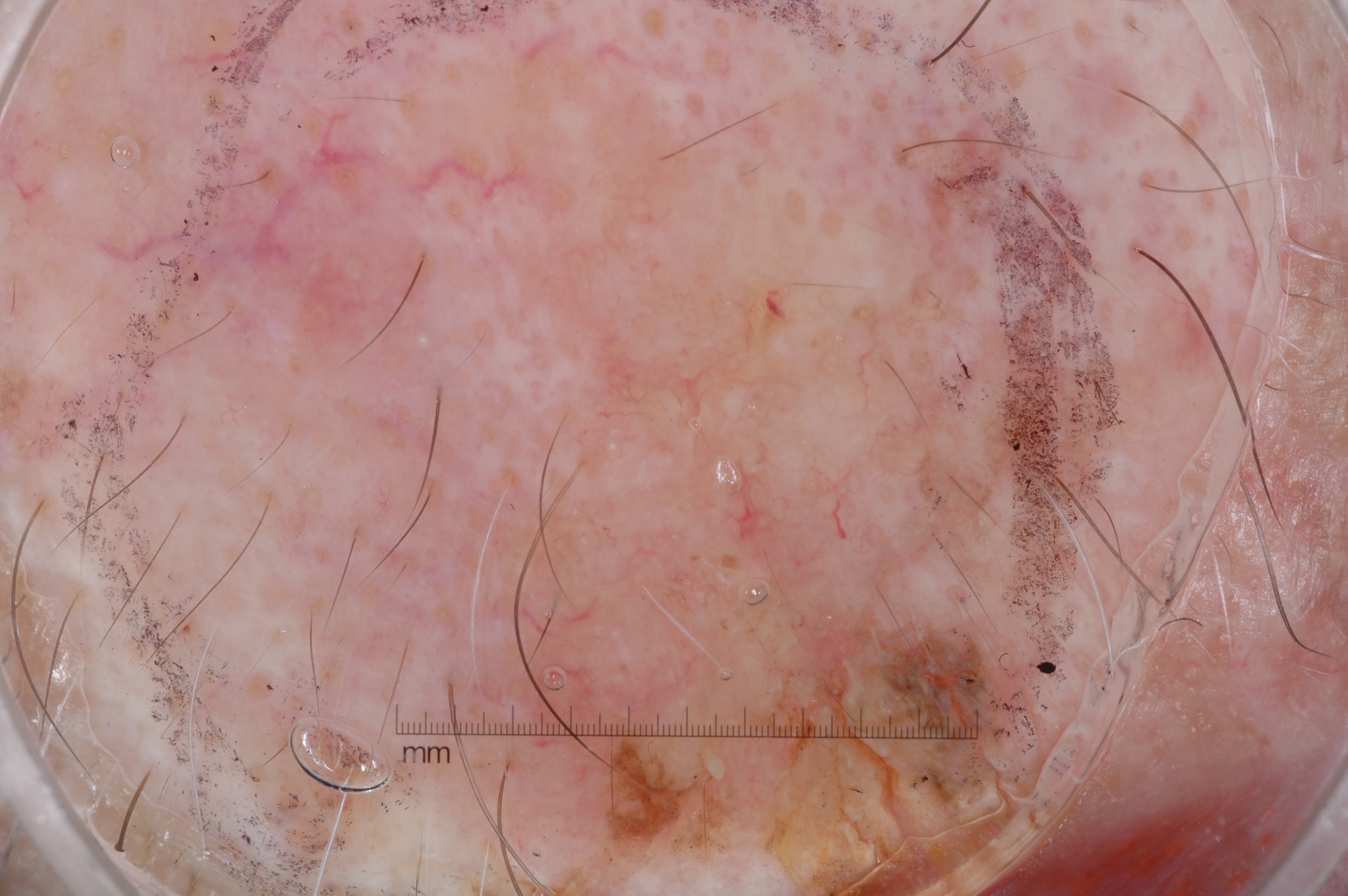A female subject about 85 years old or older. A skin lesion imaged with a dermatoscope. The lesion takes up about 67% of the image. Dermoscopy demonstrates no negative network, pigment network, milia-like cysts, or streaks. With coordinates (x1, y1, x2, y2), the lesion occupies the region 176, 6, 1213, 893. Diagnosed as a seborrheic keratosis, a lesion of keratinocytic origin.